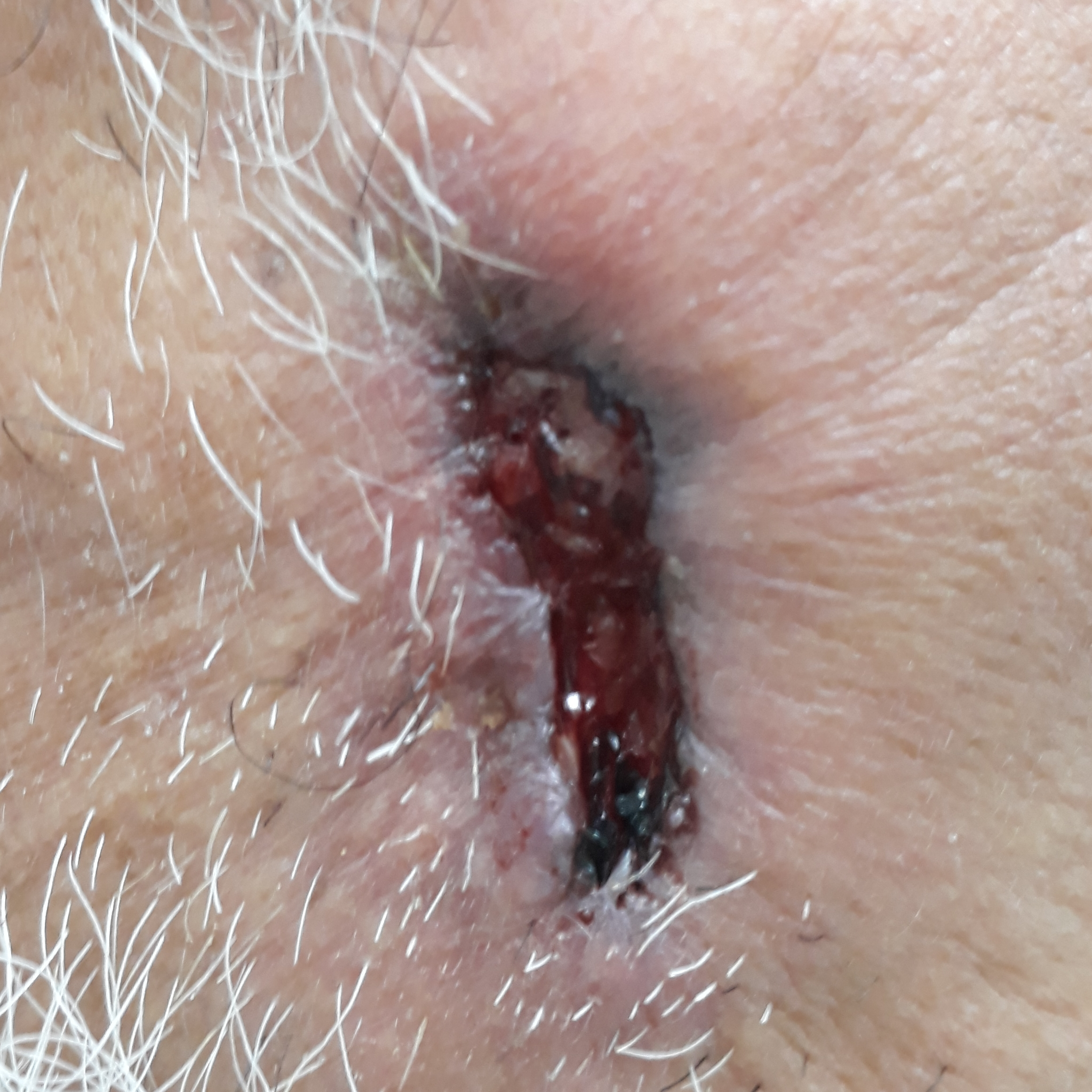exposures = pesticide exposure, no prior skin cancer (patient or family) | patient = male, in their 70s | image = clinical photo | site = the face | diameter = 40 × 5 mm | symptoms = growth, elevation, itching, bleeding, pain / no change in appearance | diagnostic label = squamous cell carcinoma (biopsy-proven).